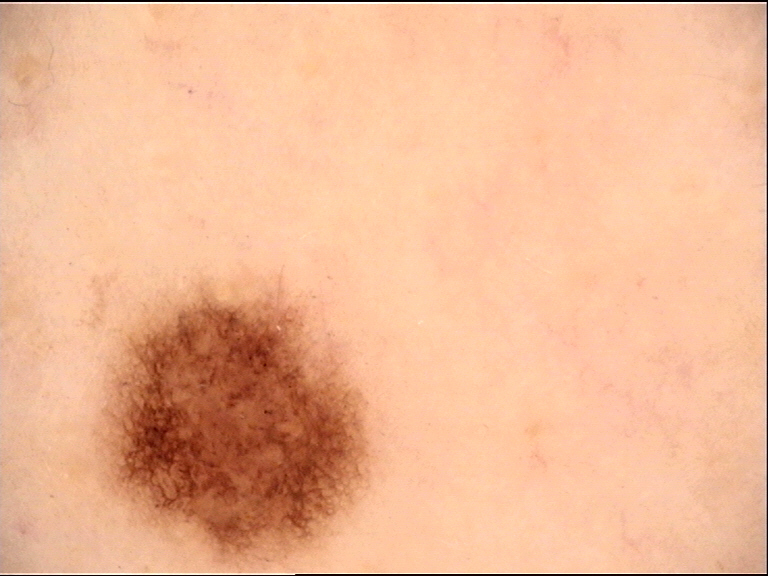class = junctional nevus (expert consensus)